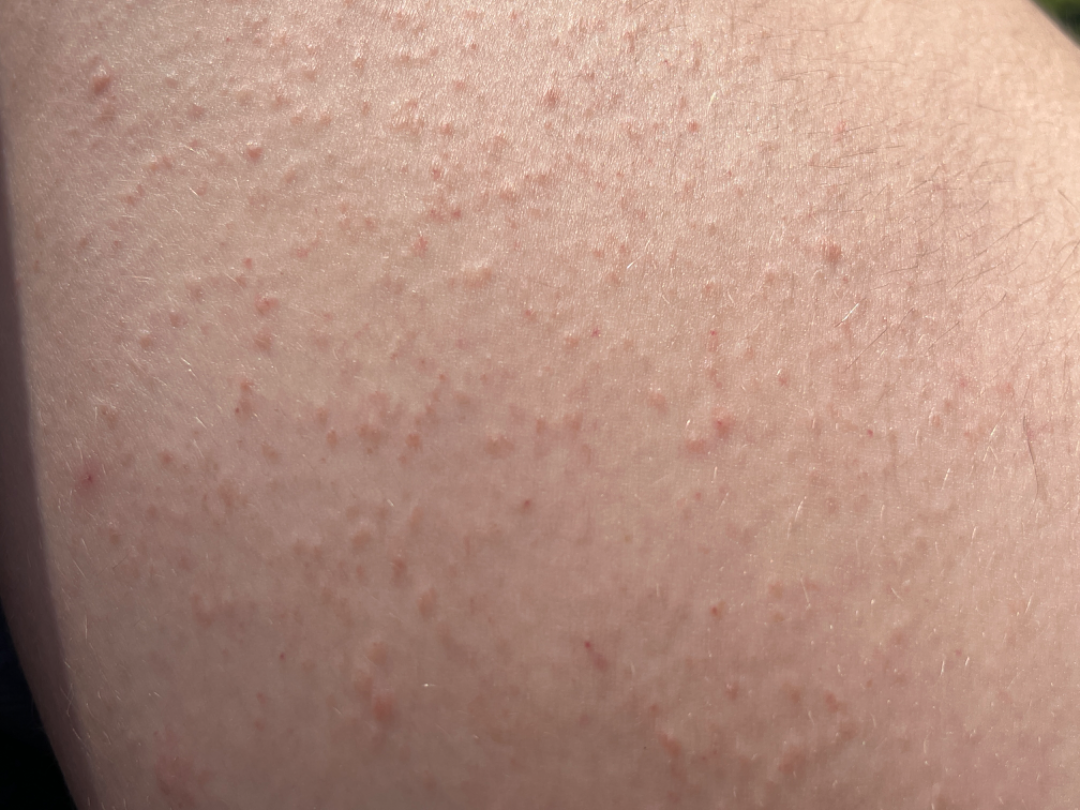Female contributor, age 18–29. Present for one to four weeks. The patient considered this a rash. The contributor reports the lesion is raised or bumpy. The leg and front of the torso are involved. The contributor reports itching. The photo was captured at an angle. On remote dermatologist review, the leading consideration is Keratosis pilaris.